The contributor is a male aged 50–59; self-categorized by the patient as a rash; the affected area is the head or neck and front of the torso; close-up view; the patient also reports shortness of breath and fatigue; reported lesion symptoms include itching, bothersome appearance and enlargement; the lesion is described as flat: 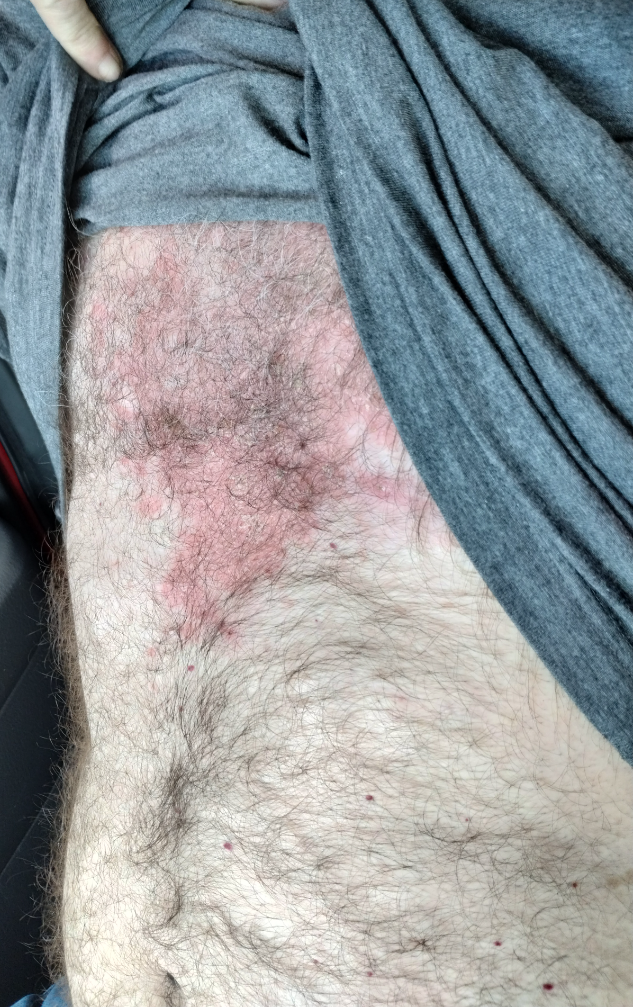differential diagnosis = the leading impression is Seborrheic Dermatitis; a more distant consideration is Psoriasis; less probable is Eczema.